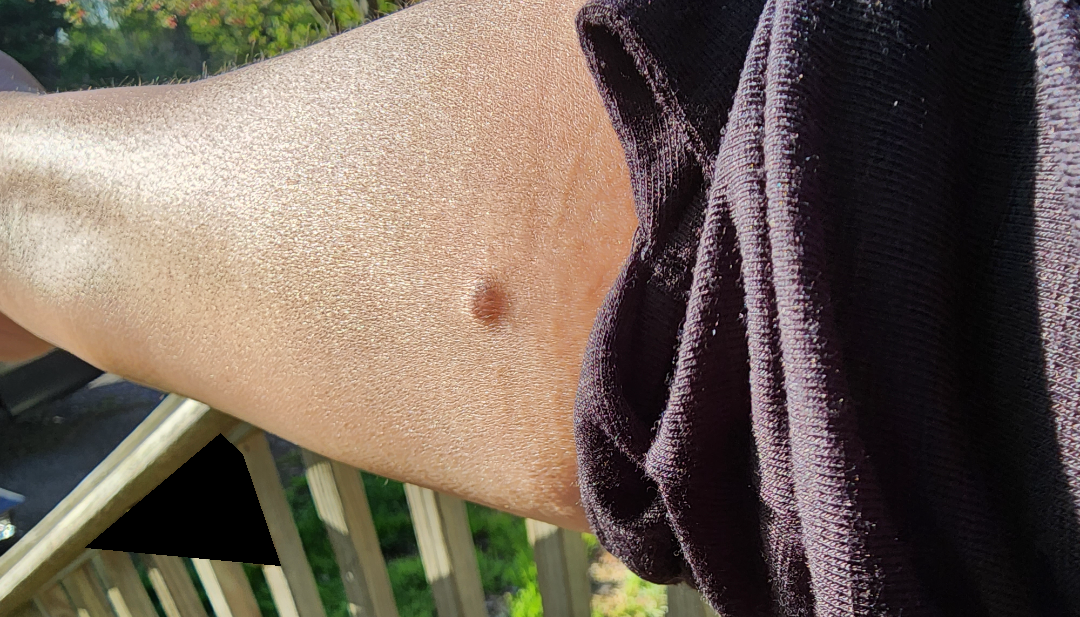Findings:
- clinical impression — the differential is split between Dermatofibroma and Neoplasm of uncertain behavior of skin of arm